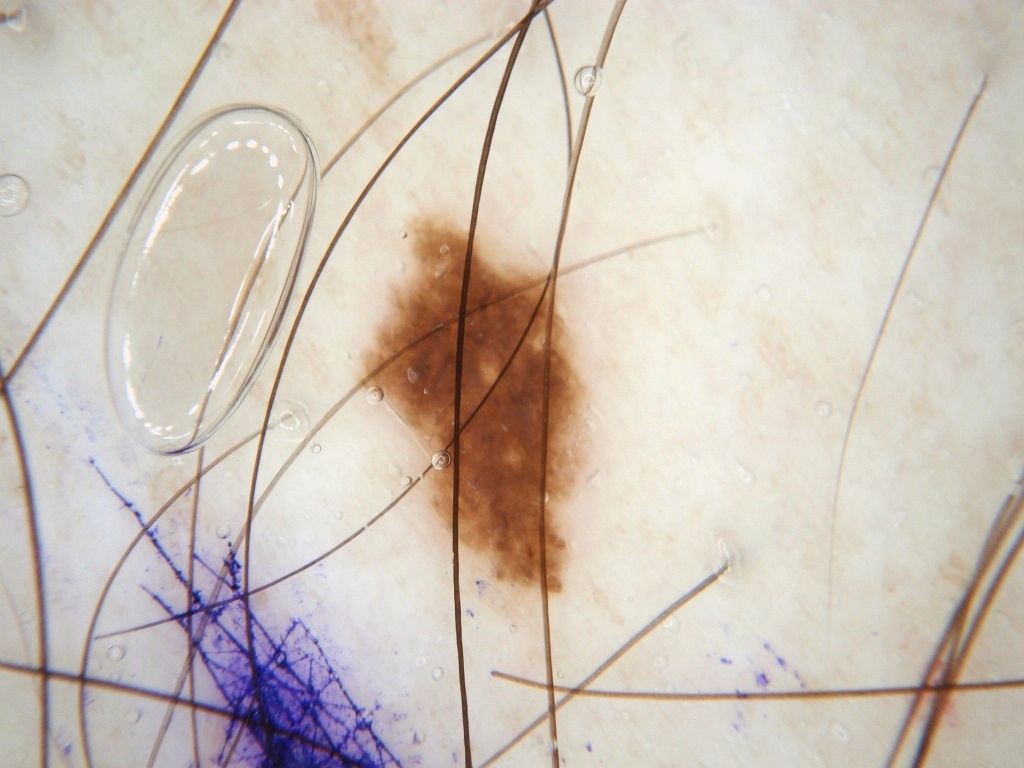A male subject approximately 40 years of age. A dermoscopic close-up of a skin lesion. Dermoscopic examination shows globules. The lesion occupies the region bbox=[338, 198, 600, 618]. Consistent with a melanocytic nevus.